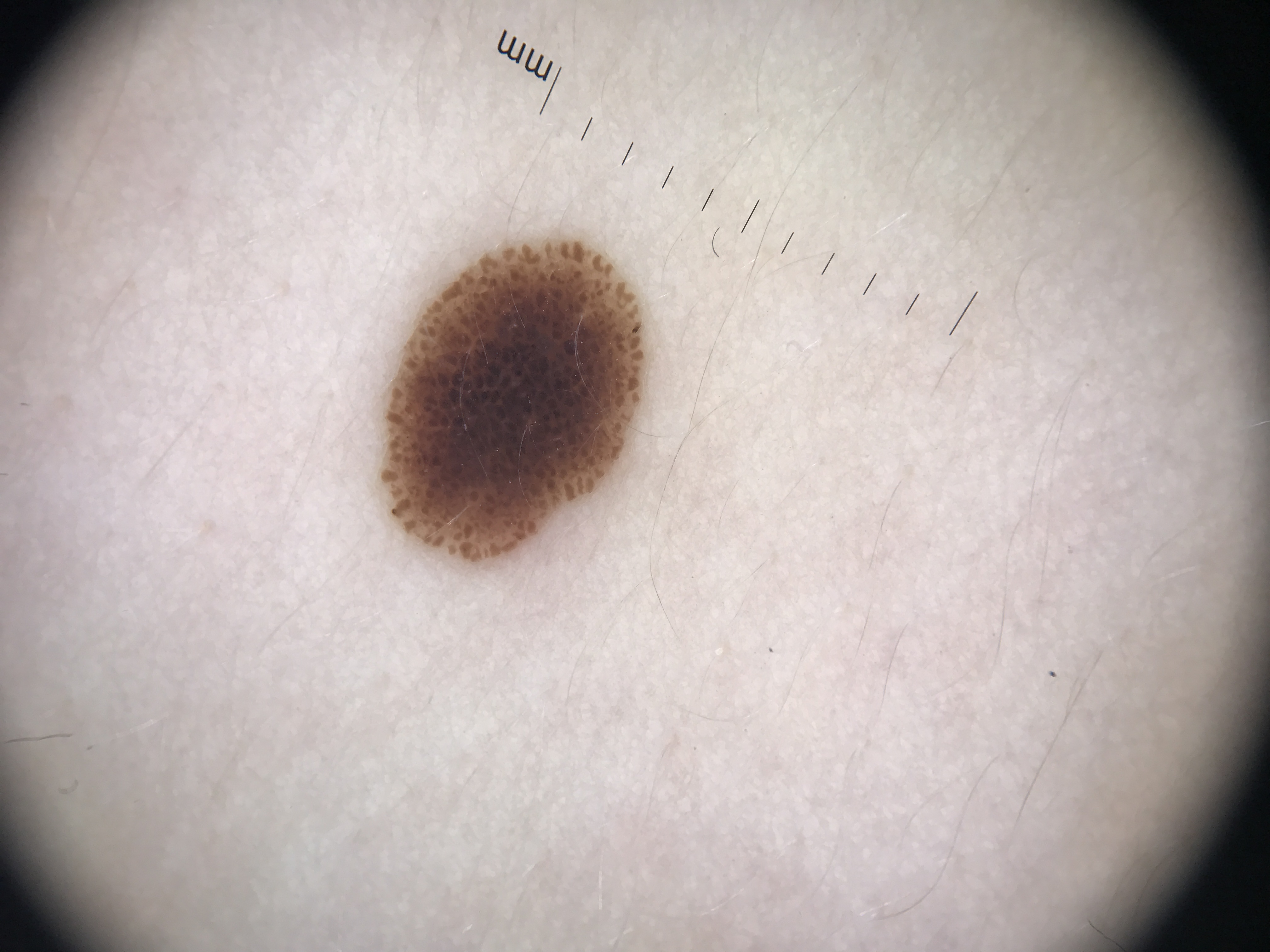The morphology is that of a banal lesion.
Labeled as a junctional nevus.